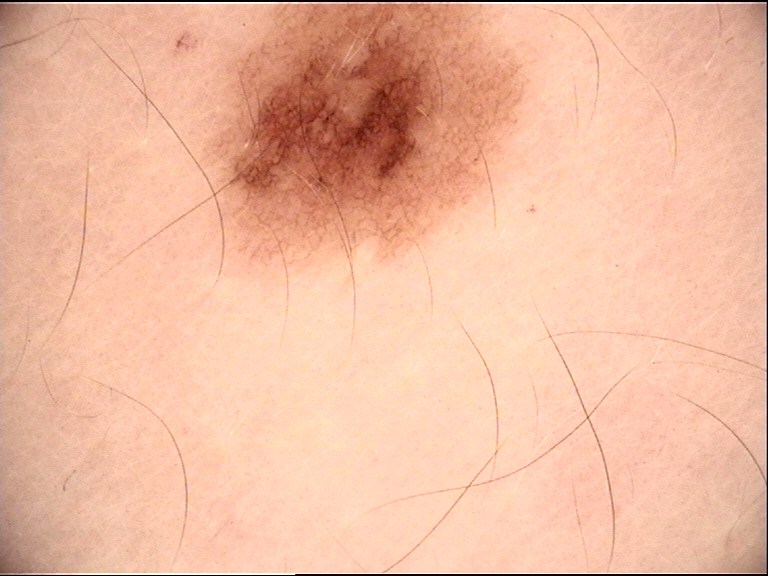The diagnostic label was a dysplastic junctional nevus.